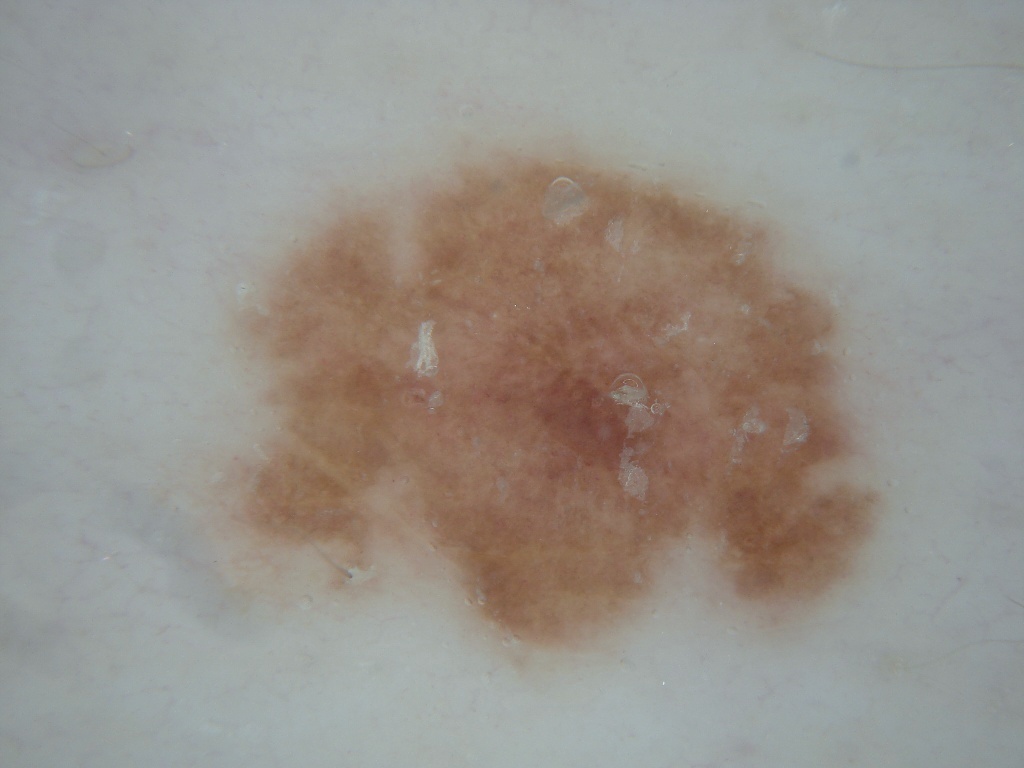Q: How was this image acquired?
A: dermoscopy of a skin lesion
Q: Patient demographics?
A: female, aged 53-57
Q: What dermoscopic features are present?
A: globules and milia-like cysts; absent: negative network, streaks, and pigment network
Q: What is the lesion's bounding box?
A: [213, 149, 884, 661]
Q: What did the assessment conclude?
A: a melanocytic nevus